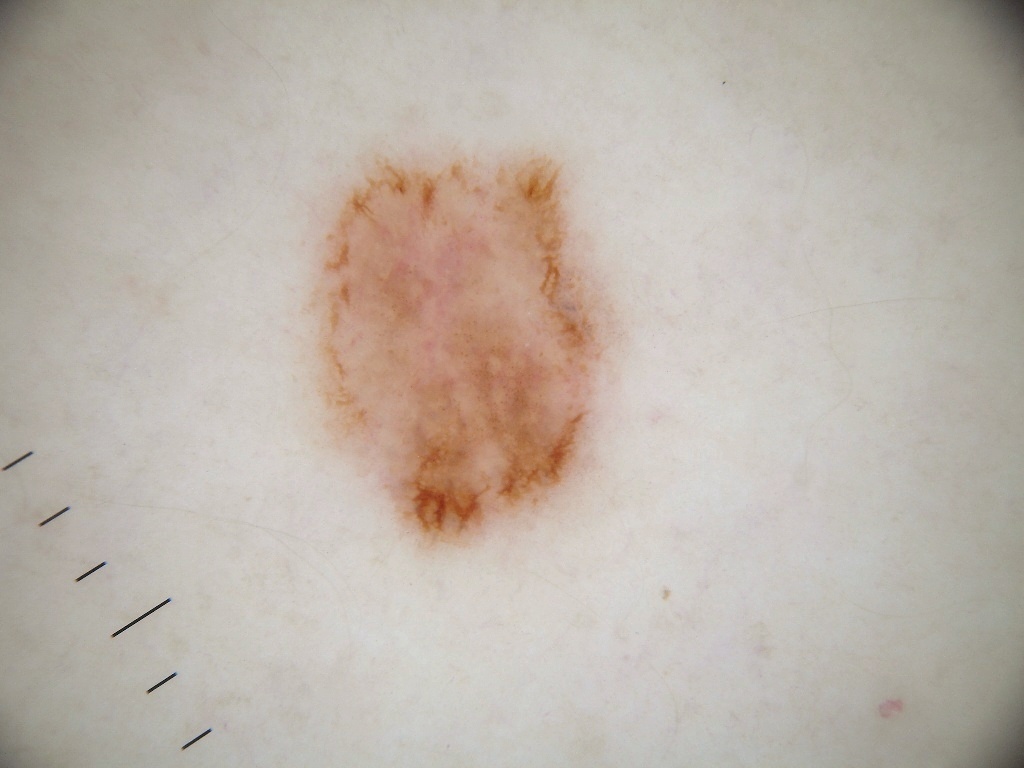{
  "image": {
    "modality": "dermoscopy"
  },
  "patient": {
    "sex": "female",
    "age_approx": 35
  },
  "dermoscopic_features": {
    "present": [
      "pigment network"
    ],
    "absent": [
      "streaks",
      "negative network",
      "globules",
      "milia-like cysts"
    ]
  },
  "lesion_location": {
    "bbox_xyxy": [
      305,
      143,
      621,
      551
    ]
  },
  "diagnosis": {
    "name": "melanocytic nevus",
    "malignancy": "benign",
    "lineage": "melanocytic",
    "provenance": "clinical"
  }
}